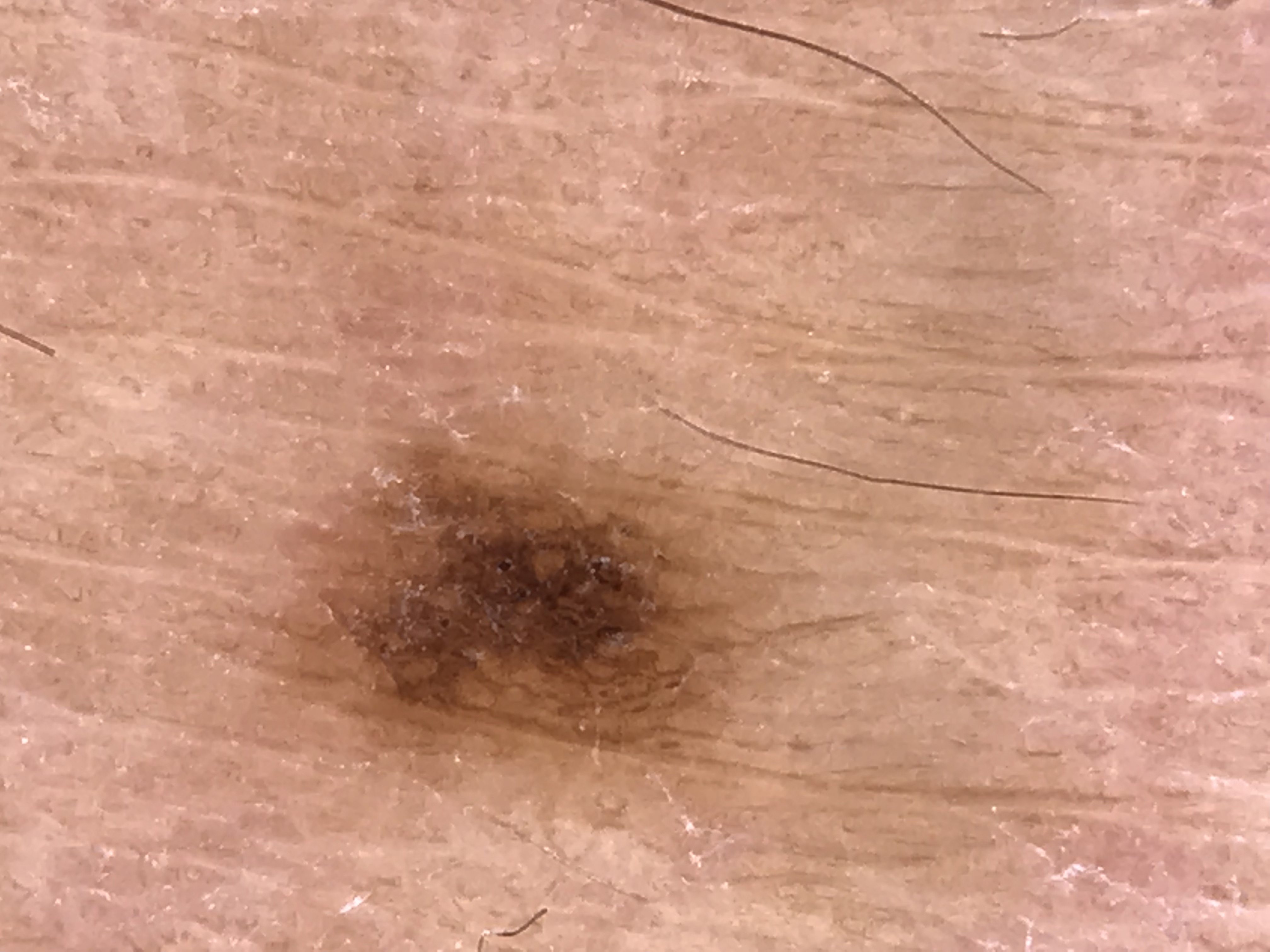Dermoscopy of a skin lesion. Classified as a benign lesion — a dysplastic junctional nevus.